The affected area is the leg. The patient described the issue as a rash. The contributor notes the condition has been present for about one day. This is a close-up image. The contributor is female. The contributor notes associated joint pain. Reported lesion symptoms include burning, pain and bothersome appearance. Texture is reported as flat — 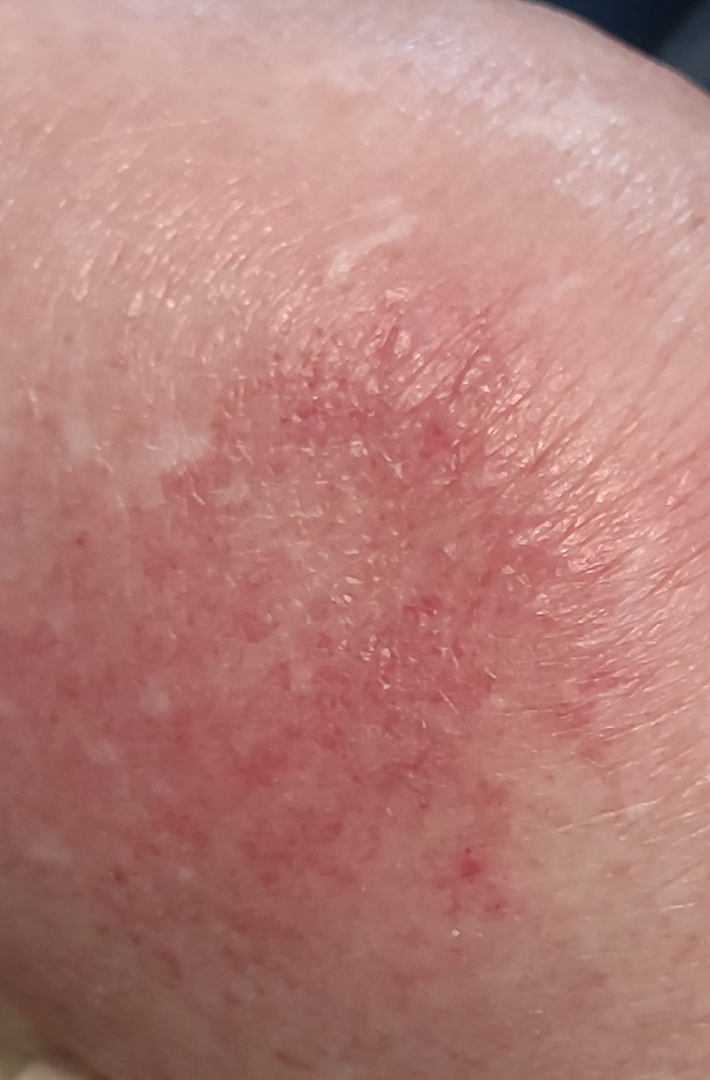* assessment: could not be assessed